A dermoscopy image of a single skin lesion — 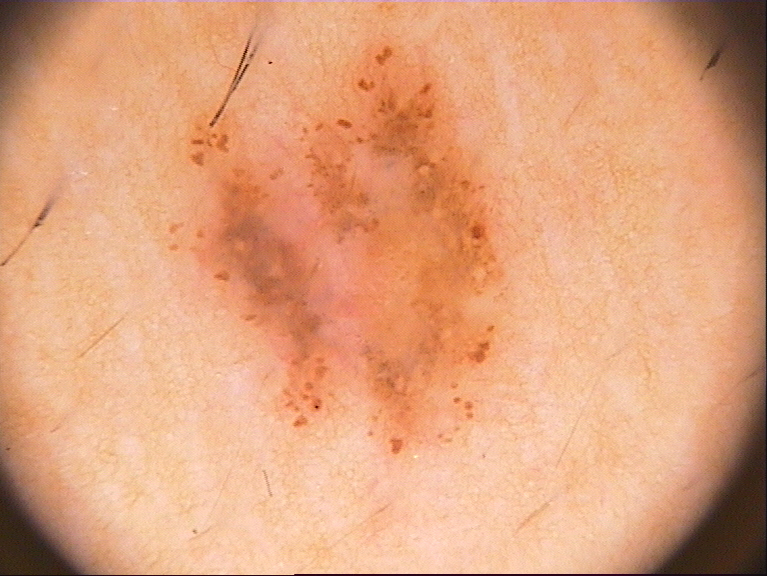{"lesion_location": {"bbox_xyxy": [166, 37, 510, 457]}, "diagnosis": {"malignancy": "benign", "provenance": "clinical"}}